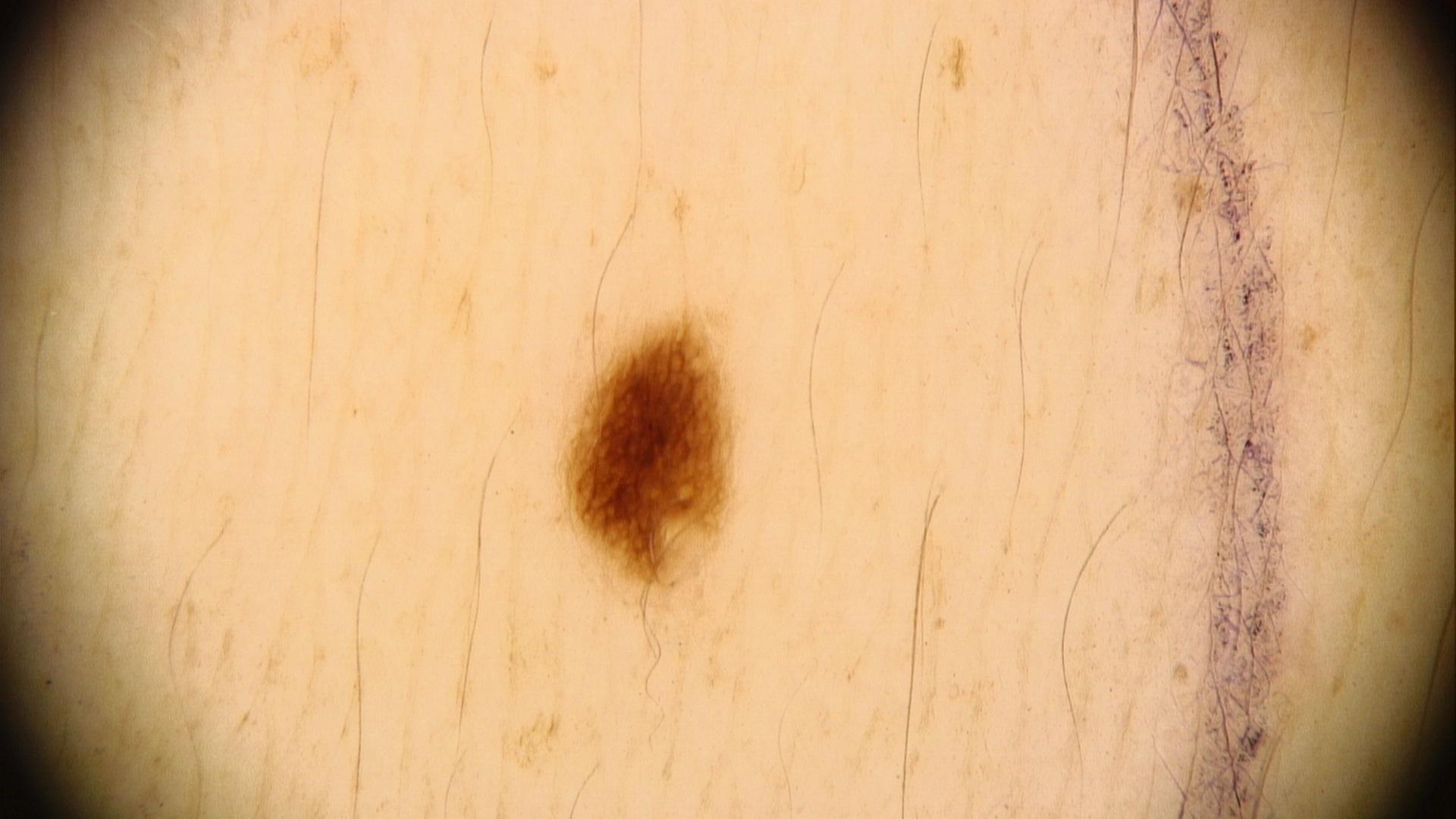Case:
• modality · contact-polarized dermoscopy
• patient · female, about 35 years old
• anatomic site · a lower extremity
• impression · Nevus